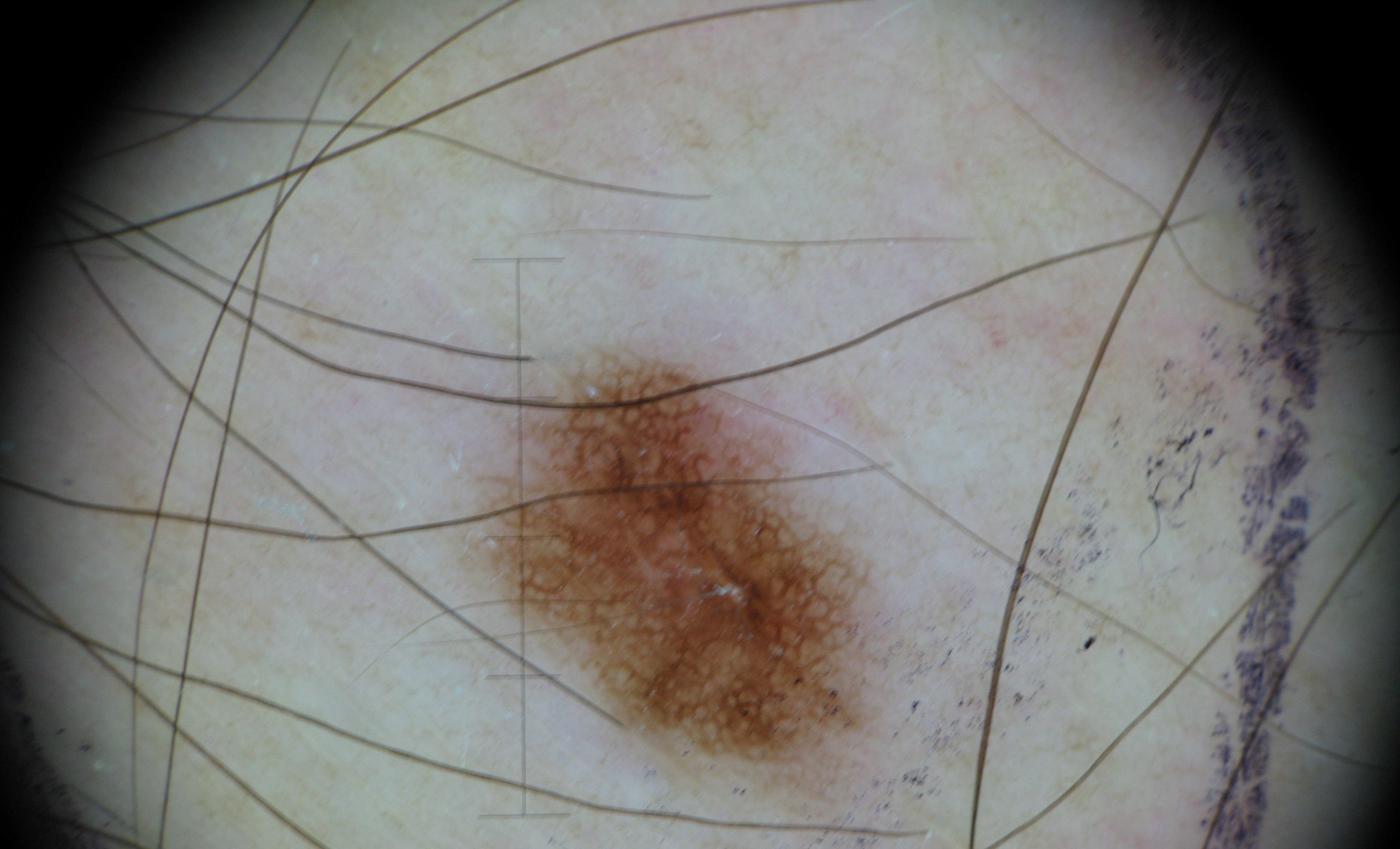A dermatoscopic image of a skin lesion.
Labeled as a banal lesion — a junctional nevus.